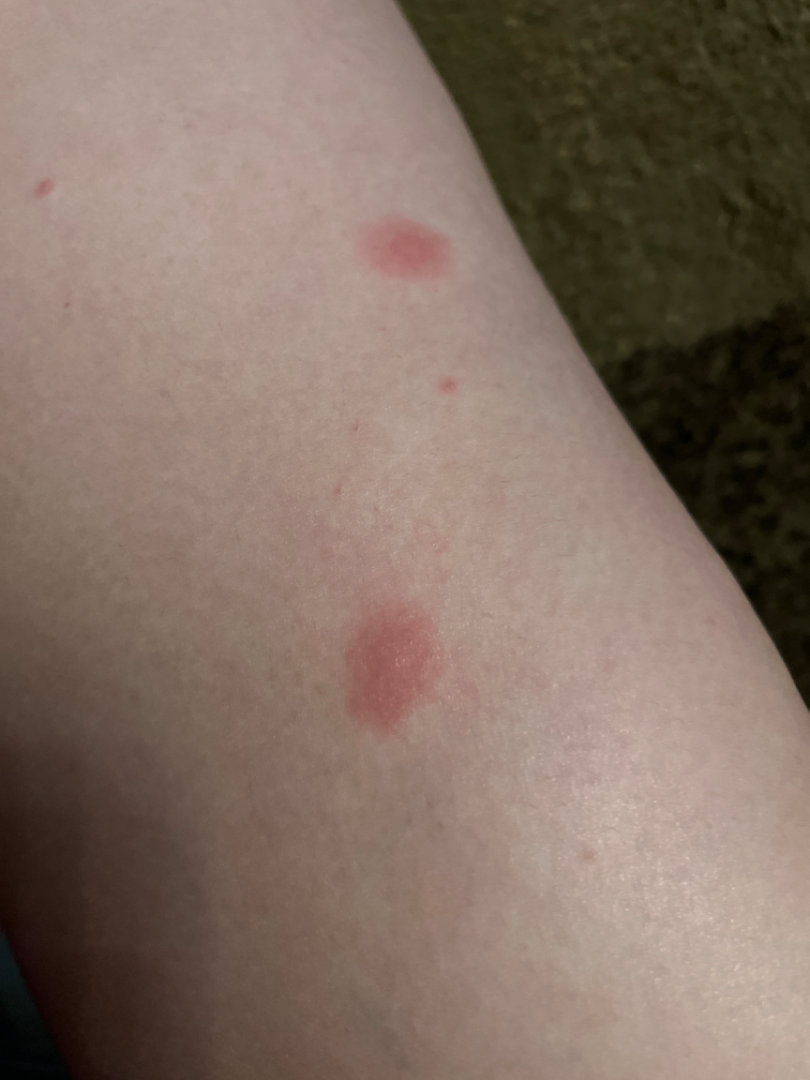The skin condition could not be confidently assessed from this image.
The subject is a female aged 18–29.
Located on the back of the torso, front of the torso, arm and leg.
A close-up photograph.